A dermoscopic image of a skin lesion:
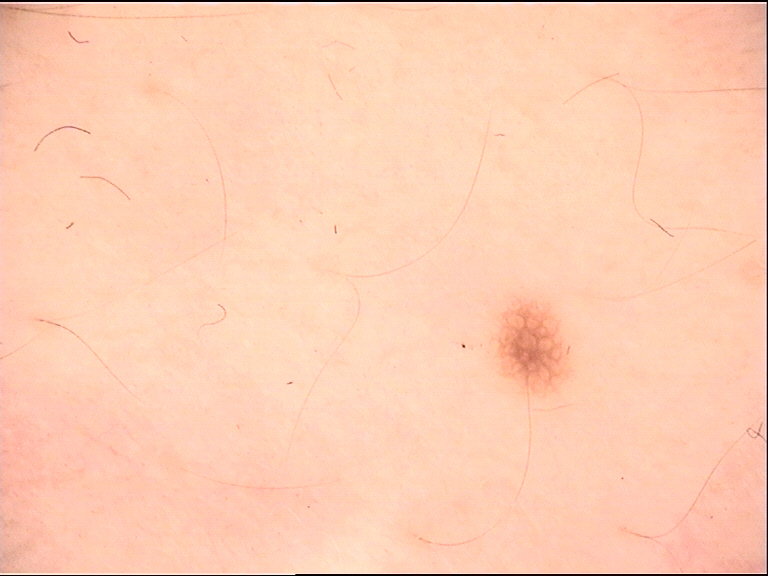label: dysplastic junctional nevus (expert consensus).